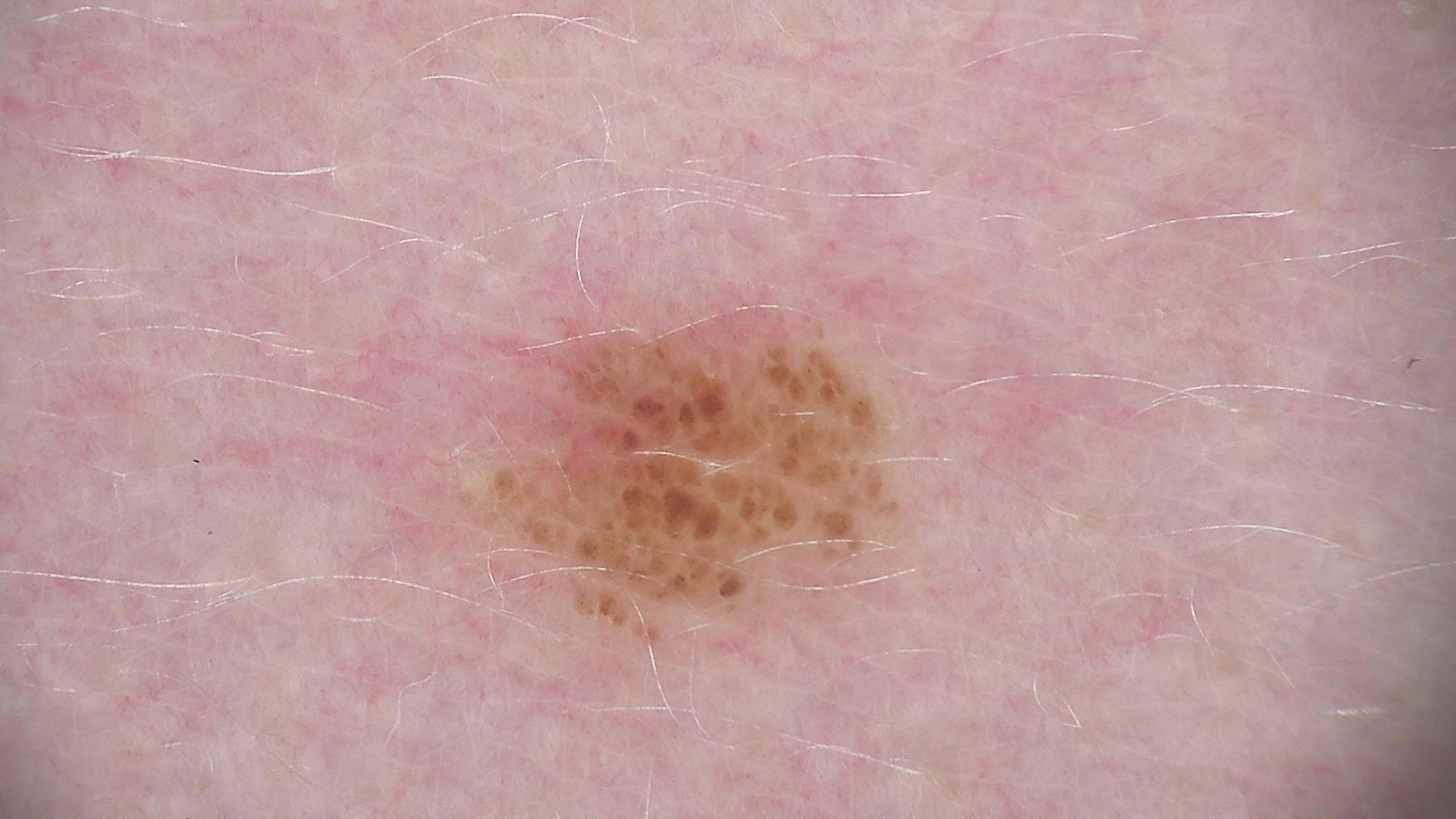  diagnosis:
    name: dysplastic junctional nevus
    code: jd
    malignancy: benign
    super_class: melanocytic
    confirmation: expert consensus